This is a dermoscopic photograph of a skin lesion, the patient is a male aged around 50:
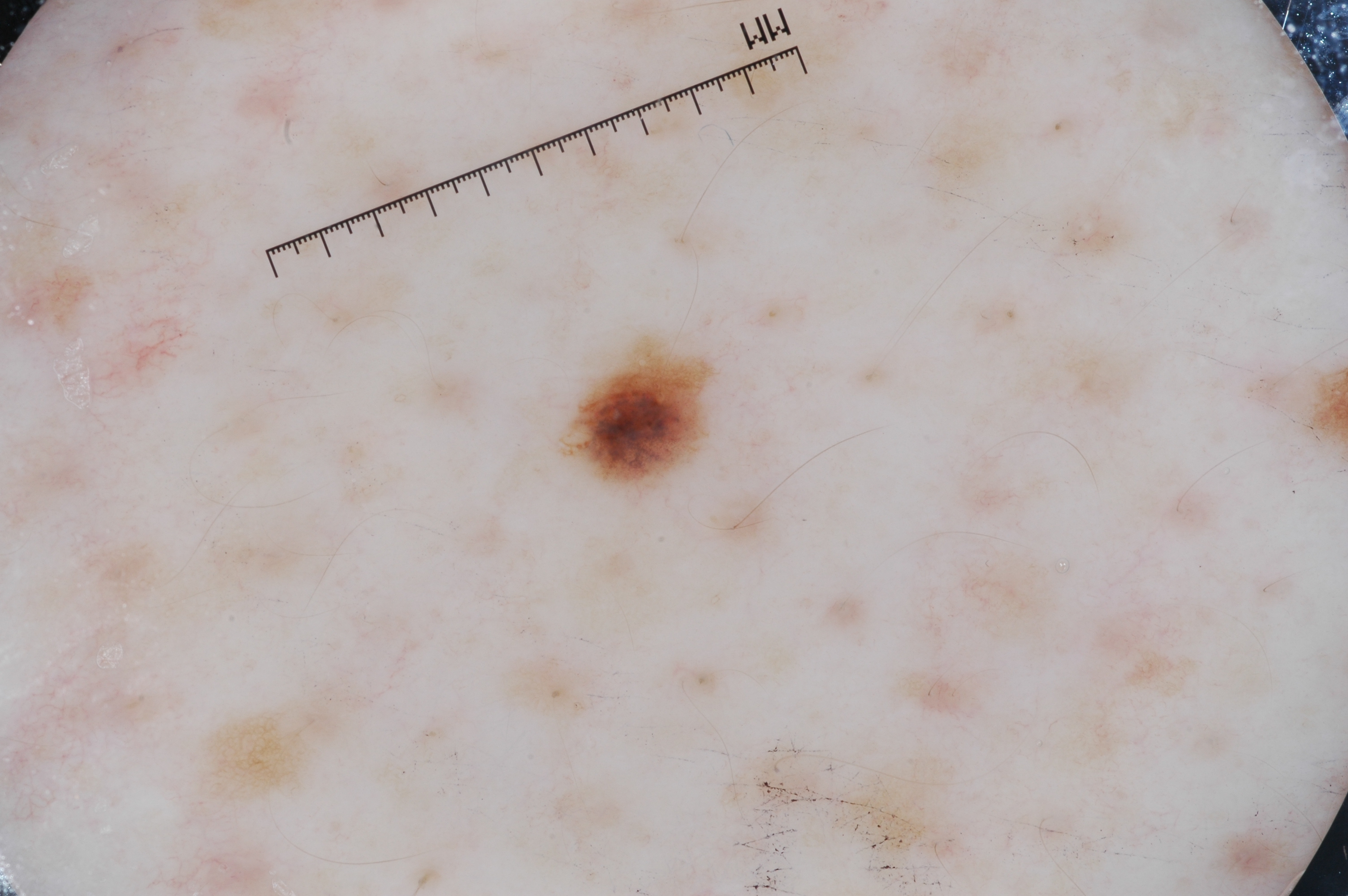Dermoscopy demonstrates pigment network; no negative network, milia-like cysts, or streaks.
With coordinates (x1, y1, x2, y2), the lesion's extent is 569/343/705/483.
Diagnosed as a melanocytic nevus, a benign skin lesion.